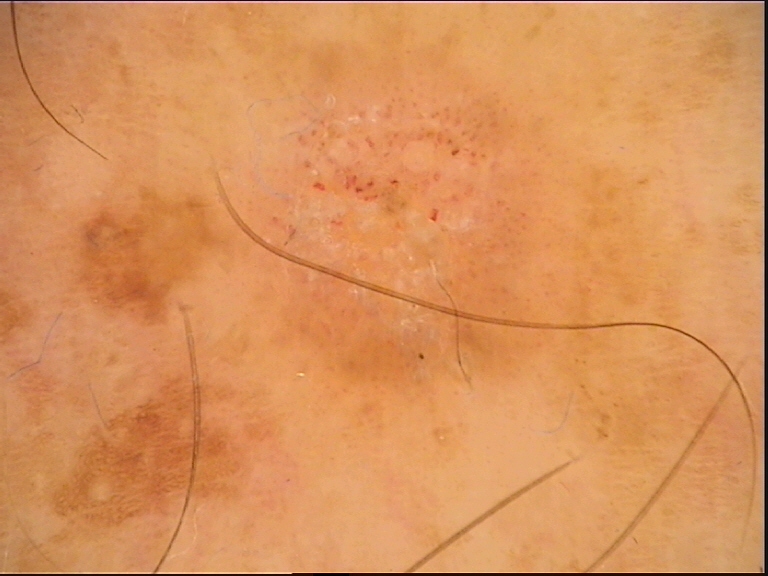Summary:
This is a keratinocytic lesion.
Conclusion:
Diagnosed as a seborrheic keratosis.